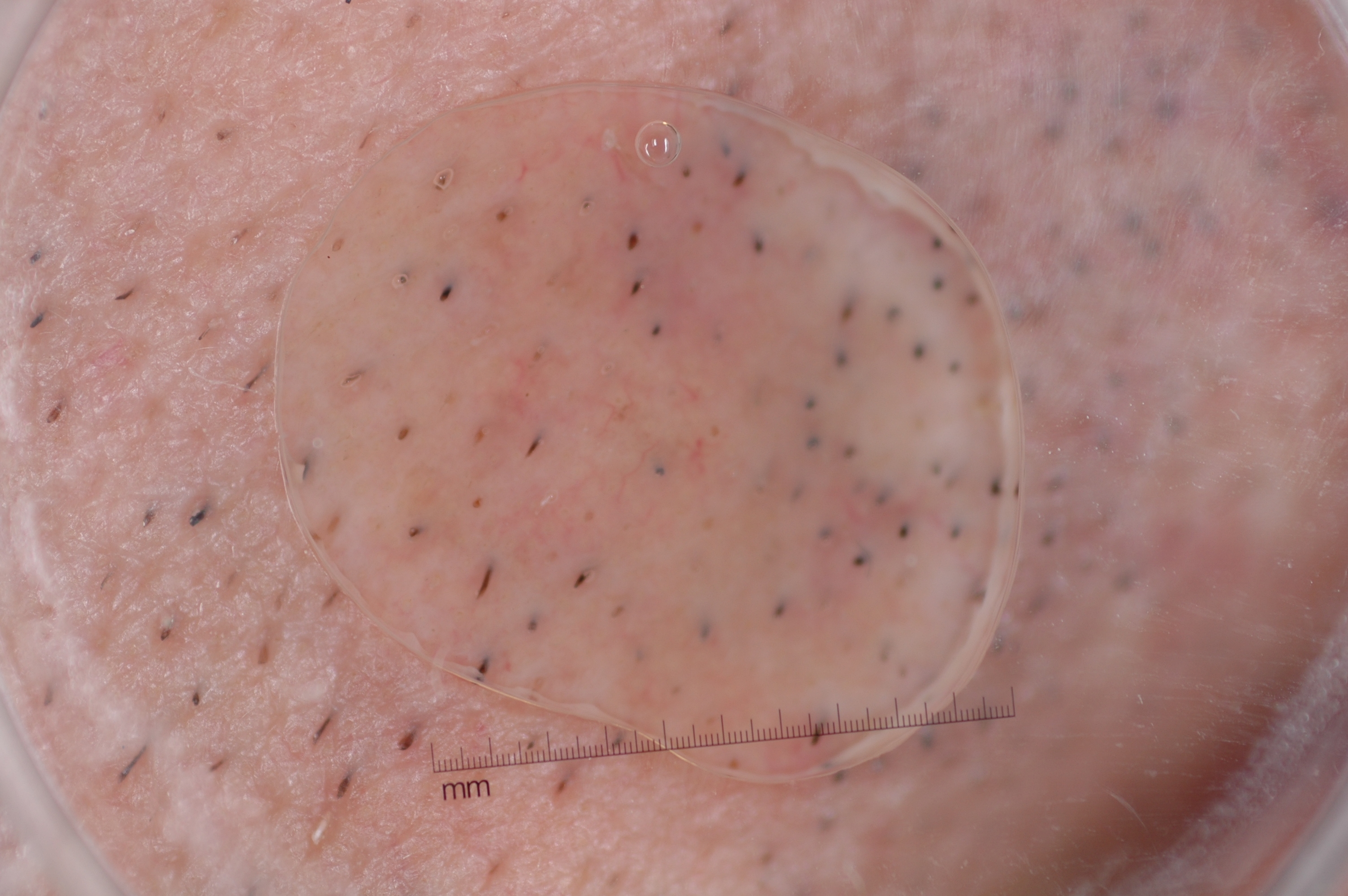| field | value |
|---|---|
| modality | dermoscopy of a skin lesion |
| lesion location | 357, 122, 981, 709 |
| diagnosis | a melanocytic nevus |